Dermoscopy of a skin lesion.
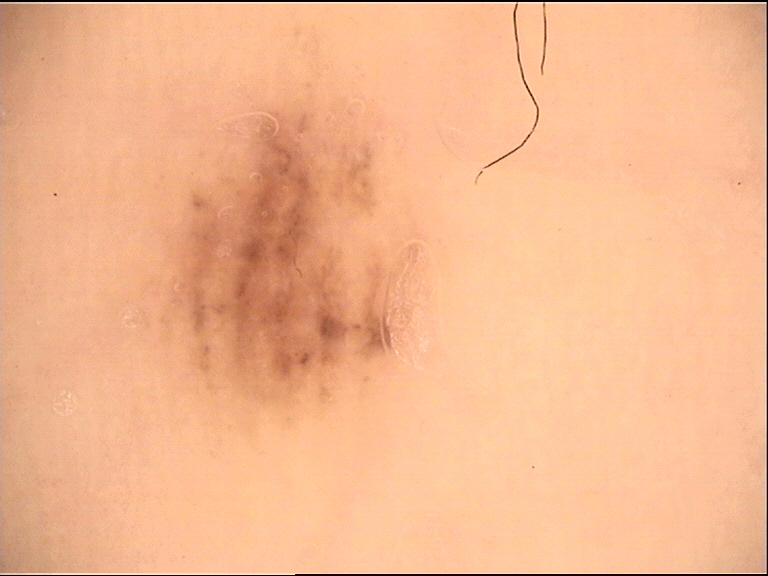Case:
* diagnostic label: acral dysplastic junctional nevus (expert consensus)